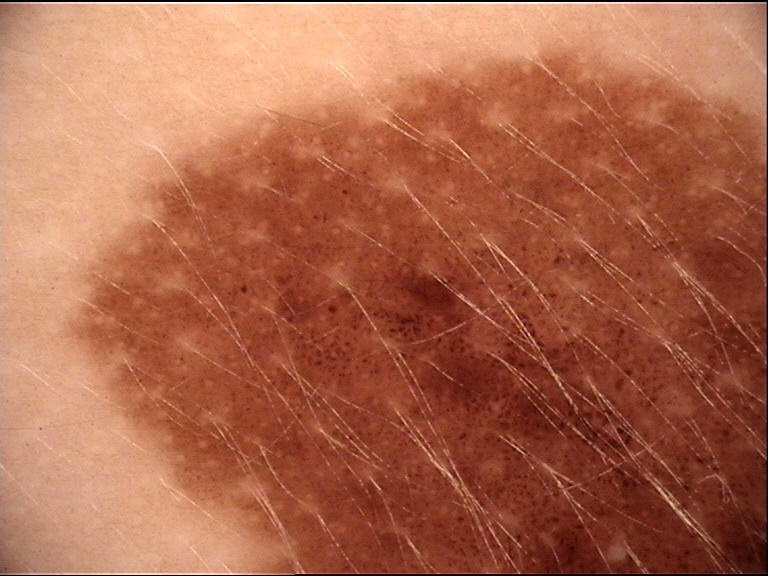image: dermatoscopy
lesion_type:
  main_class: banal
  pattern: junctional
diagnosis:
  name: congenital junctional nevus
  code: cjb
  malignancy: benign
  super_class: melanocytic
  confirmation: expert consensus